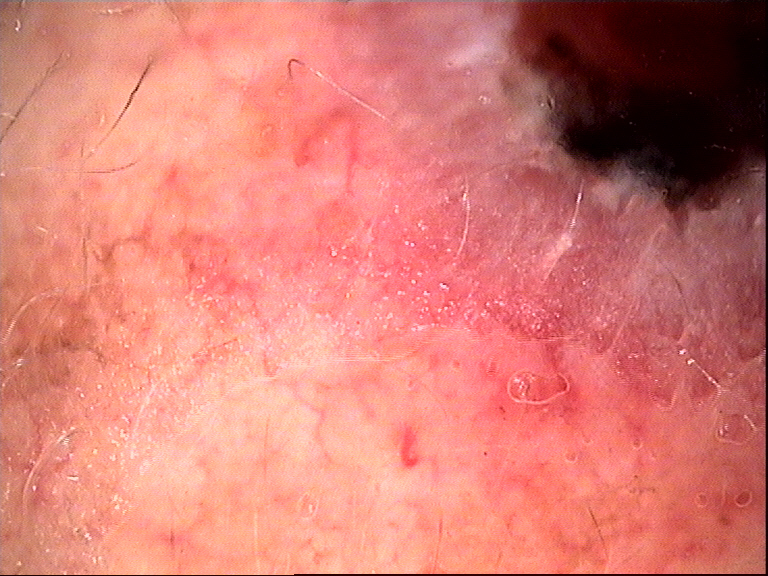image type: dermoscopy | class: basal cell carcinoma (biopsy-proven).